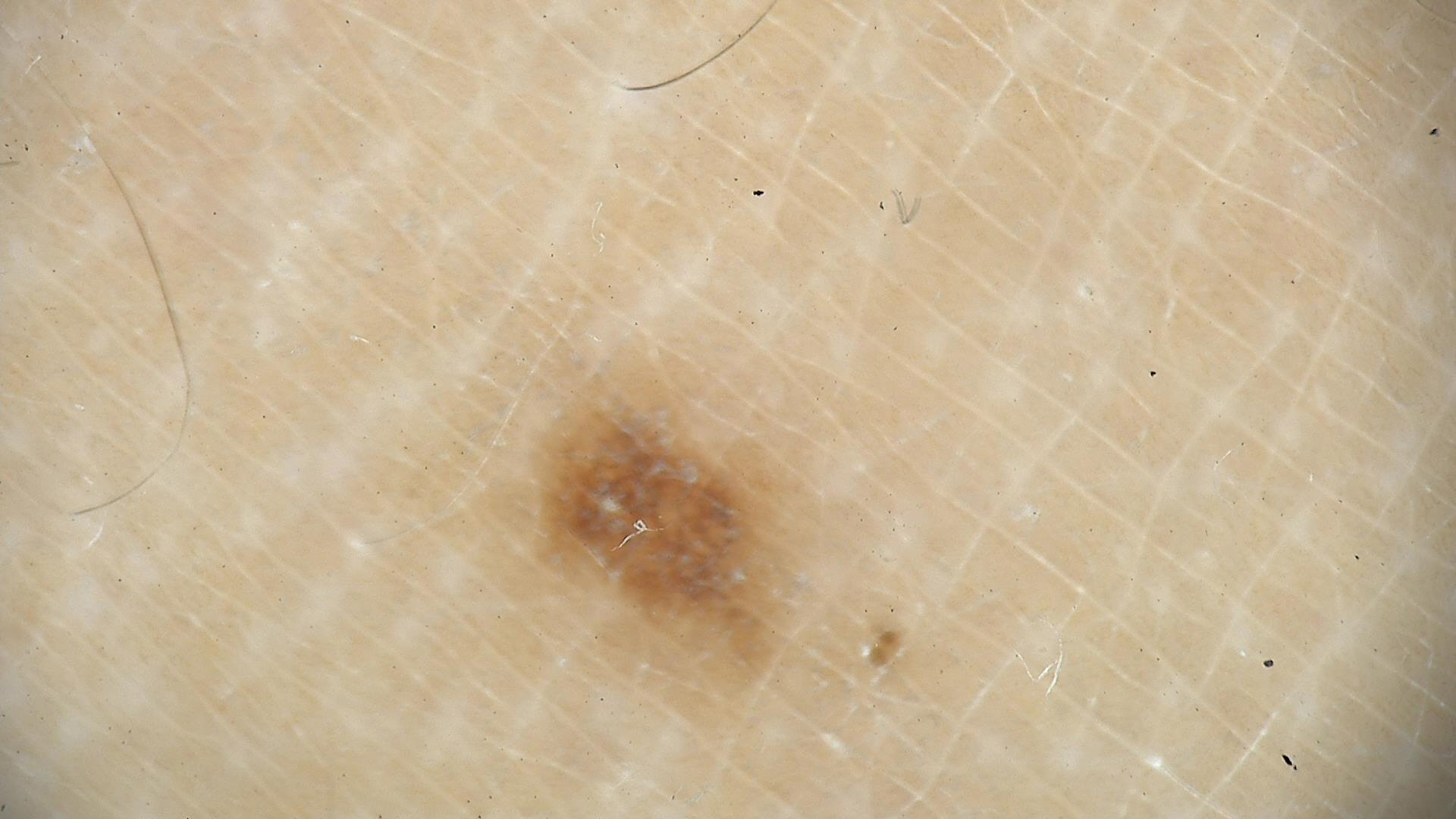image type = dermatoscopy | diagnosis = dysplastic junctional nevus (expert consensus).